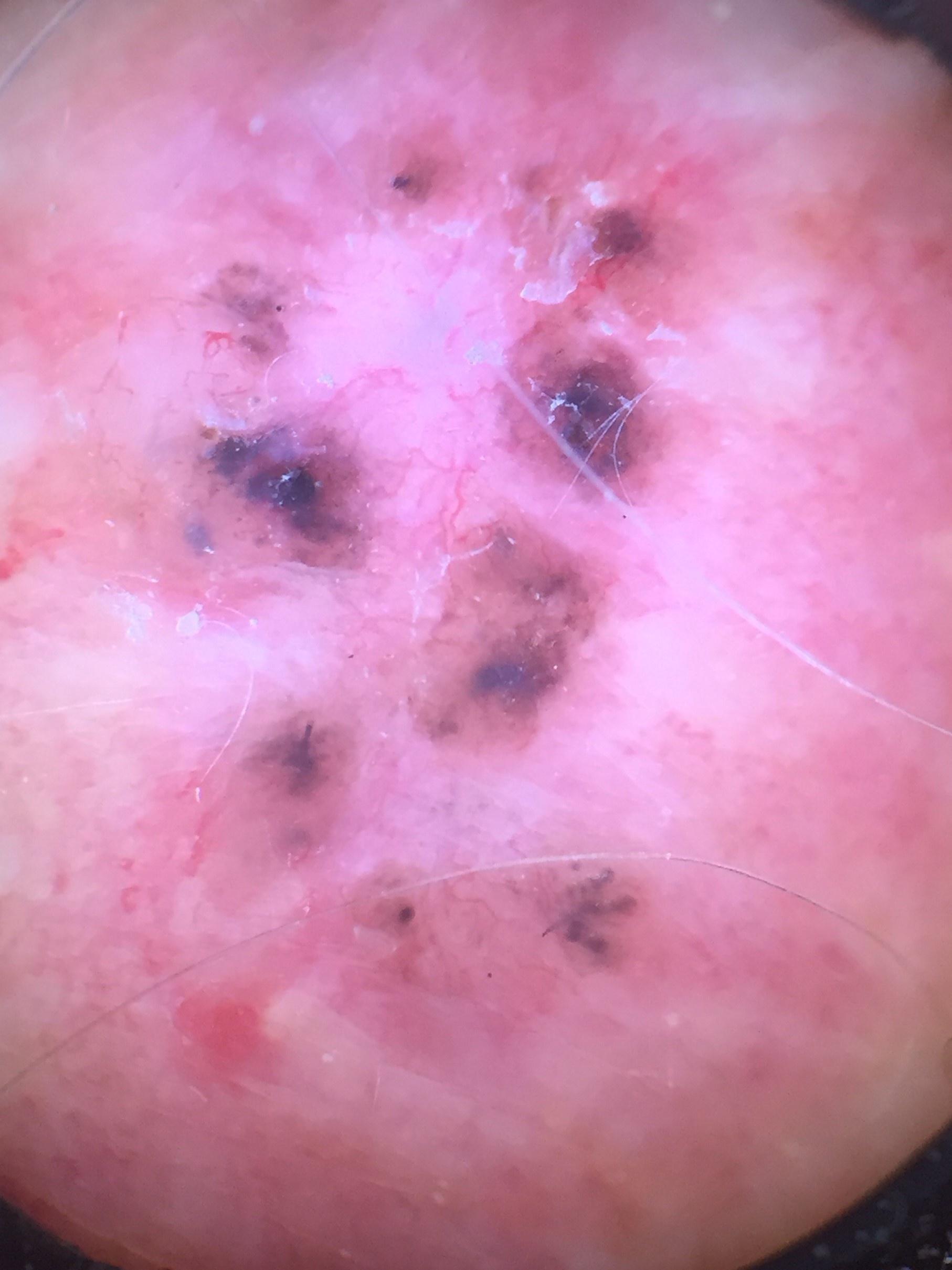Q: Any relevant melanoma history?
A: a previous melanoma
Q: Patient demographics?
A: male, approximately 80 years of age
Q: What is the patient's skin type?
A: II
Q: What is the anatomic site?
A: the posterior trunk
Q: What is the diagnosis?
A: Basal cell carcinoma (biopsy-proven)